Close-up view, the affected area is the palm, the patient is a female aged 50–59:
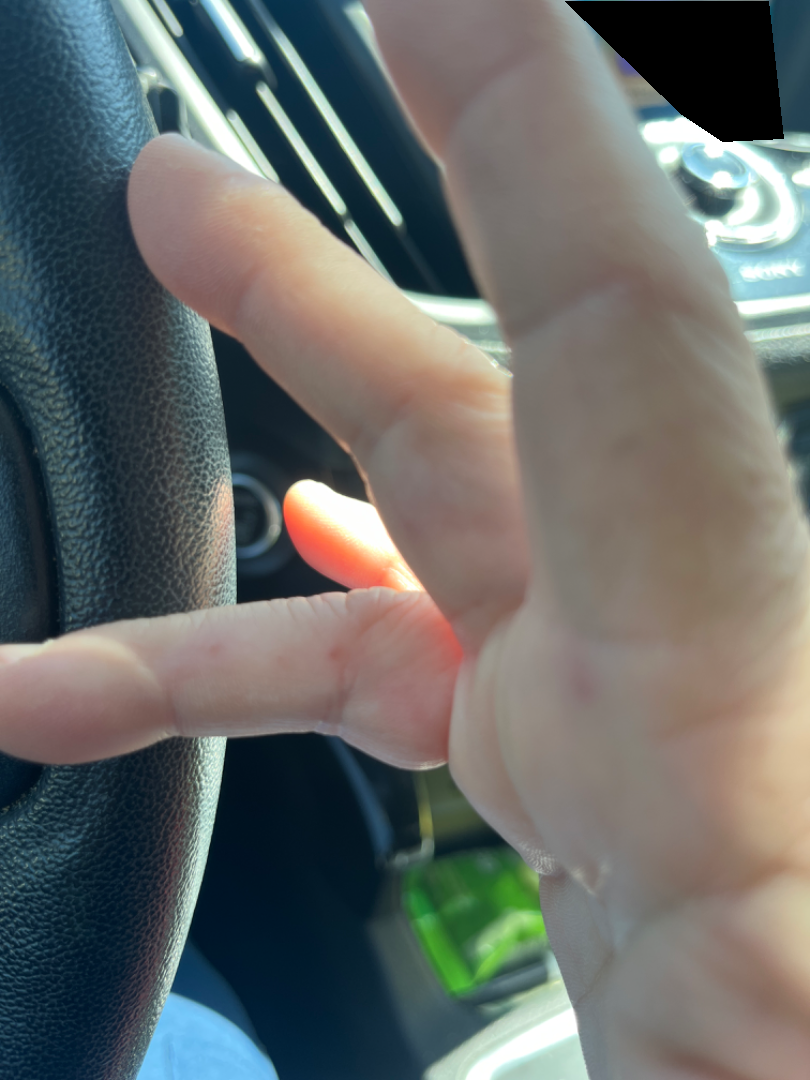| field | value |
|---|---|
| assessment | not assessable |
| systemic symptoms | fatigue |
| skin tone | self-reported Fitzpatrick phototype II; lay reviewers estimated Monk Skin Tone 1 or 2 |
| lesion texture | raised or bumpy |
| duration | about one day |
| patient-reported symptoms | pain |